A female subject 47 years of age · a smartphone photograph of a skin lesion: 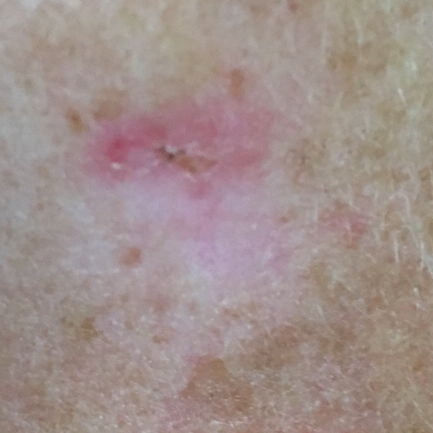Q: What is the anatomic site?
A: the face
Q: What does the patient describe?
A: itching
Q: What is this lesion?
A: actinic keratosis (biopsy-proven)